A skin lesion imaged with a dermatoscope: 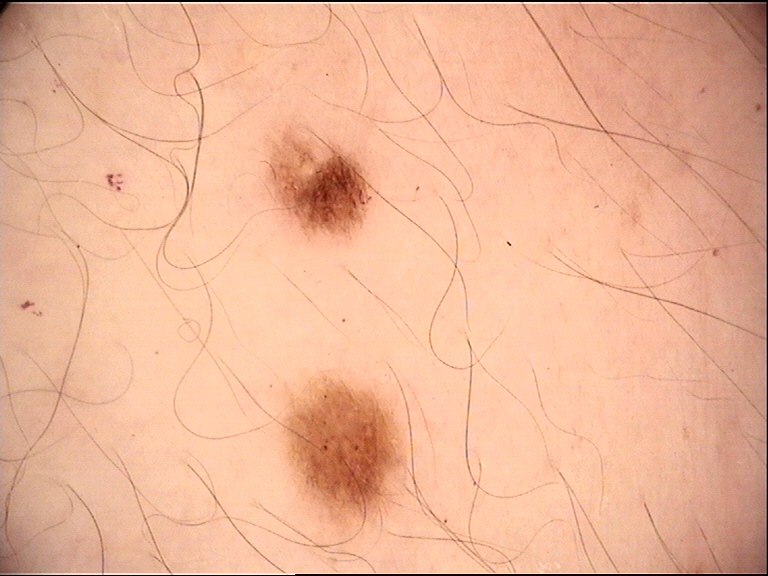assessment: dysplastic junctional nevus (expert consensus)